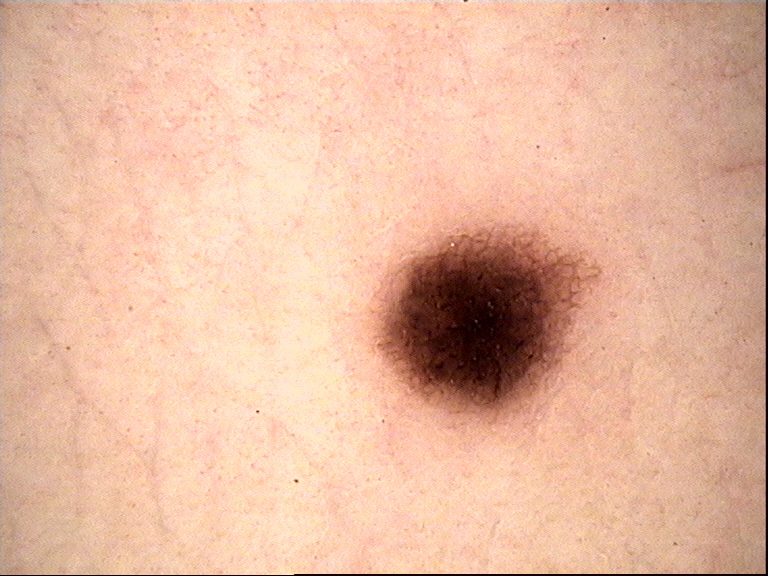The diagnostic label was a junctional nevus.